The affected area is the leg; a close-up photograph; female patient, age 18–29: 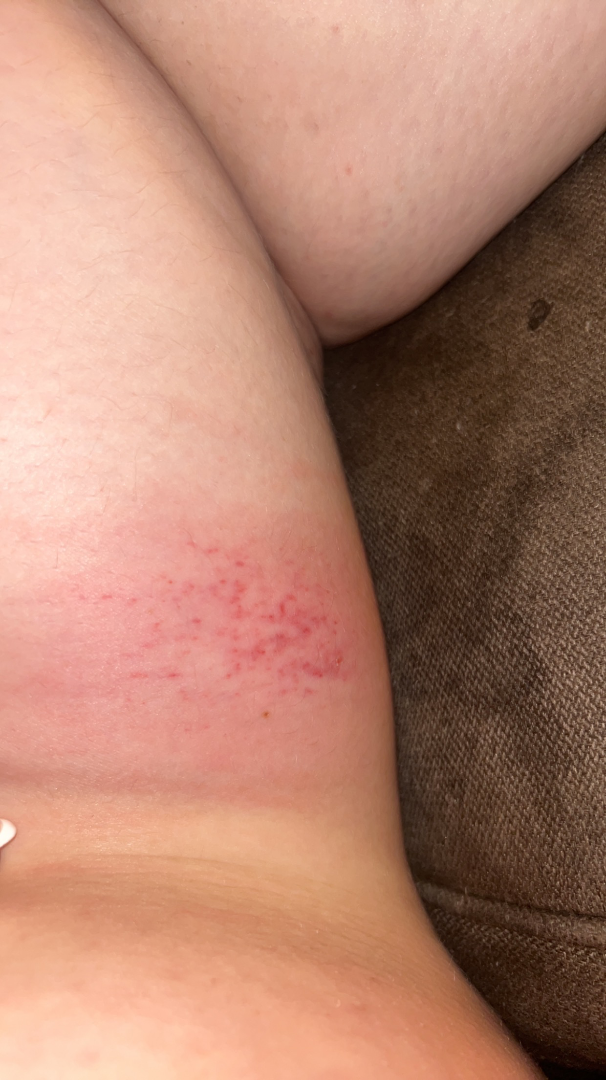Clinical context: Symptoms reported: enlargement, itching, bleeding, pain and bothersome appearance. The patient described the issue as a rash. The lesion is described as fluid-filled. Assessment: Cellulitis (considered); Traumatic petechiae (considered); Purpura (considered).